Female contributor, age 18–29. Located on the arm. This image was taken at a distance: 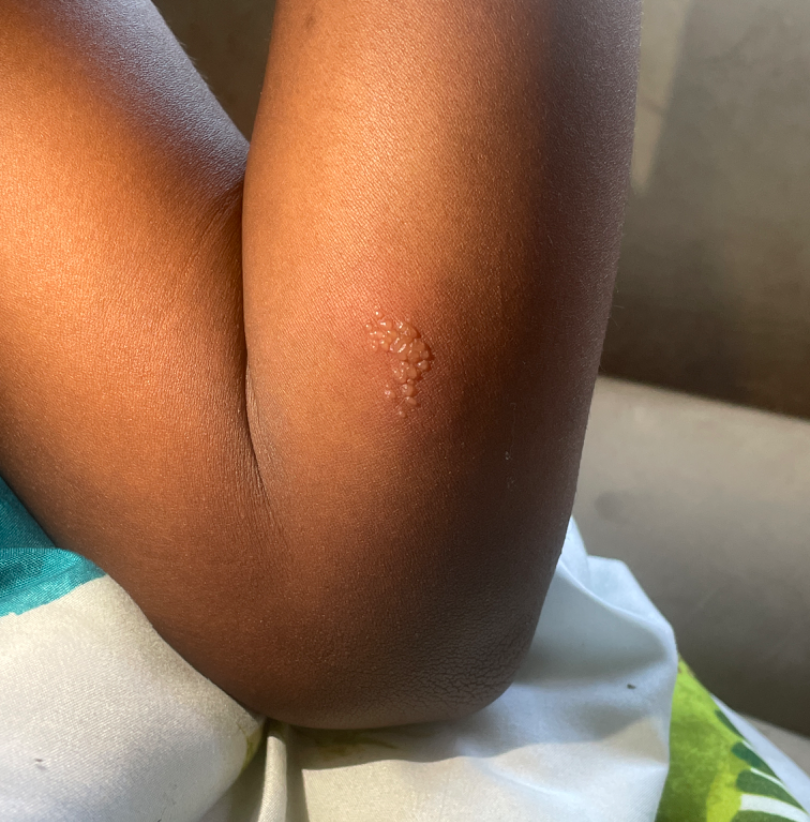dermatologist impression: Herpes Simplex (1.00).